This is a close-up image:
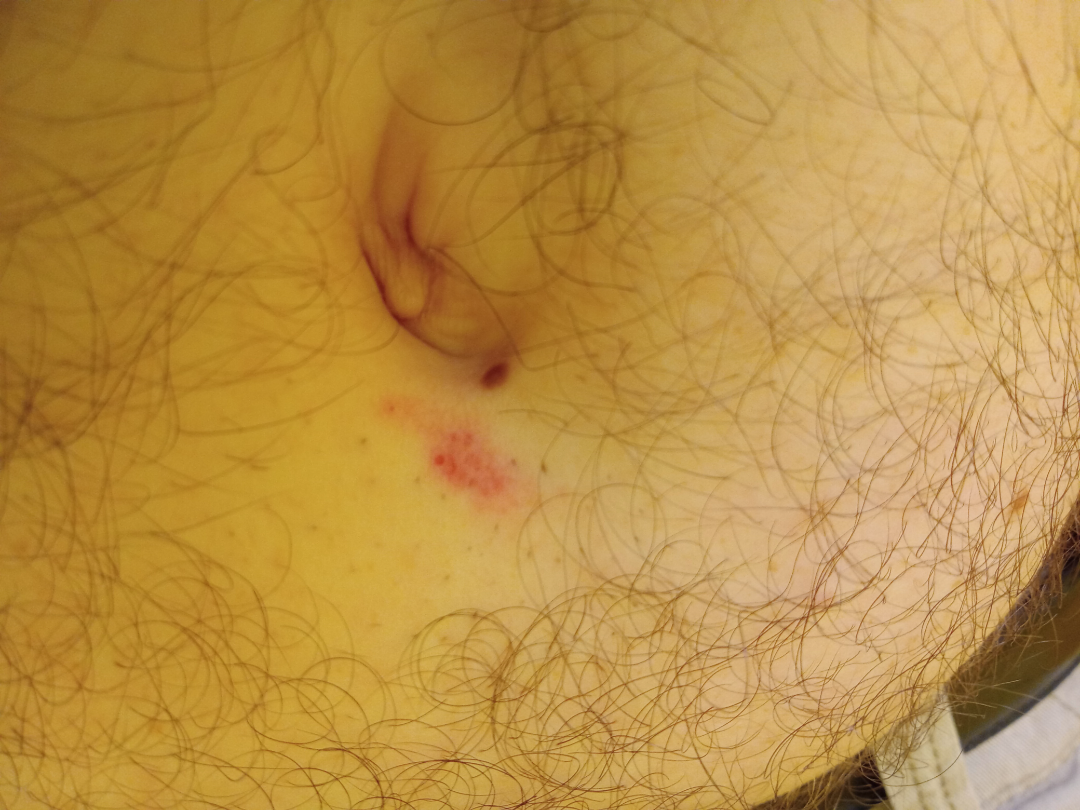assessment — not assessable.